Located on the top or side of the foot. A close-up photograph. The contributor is female — 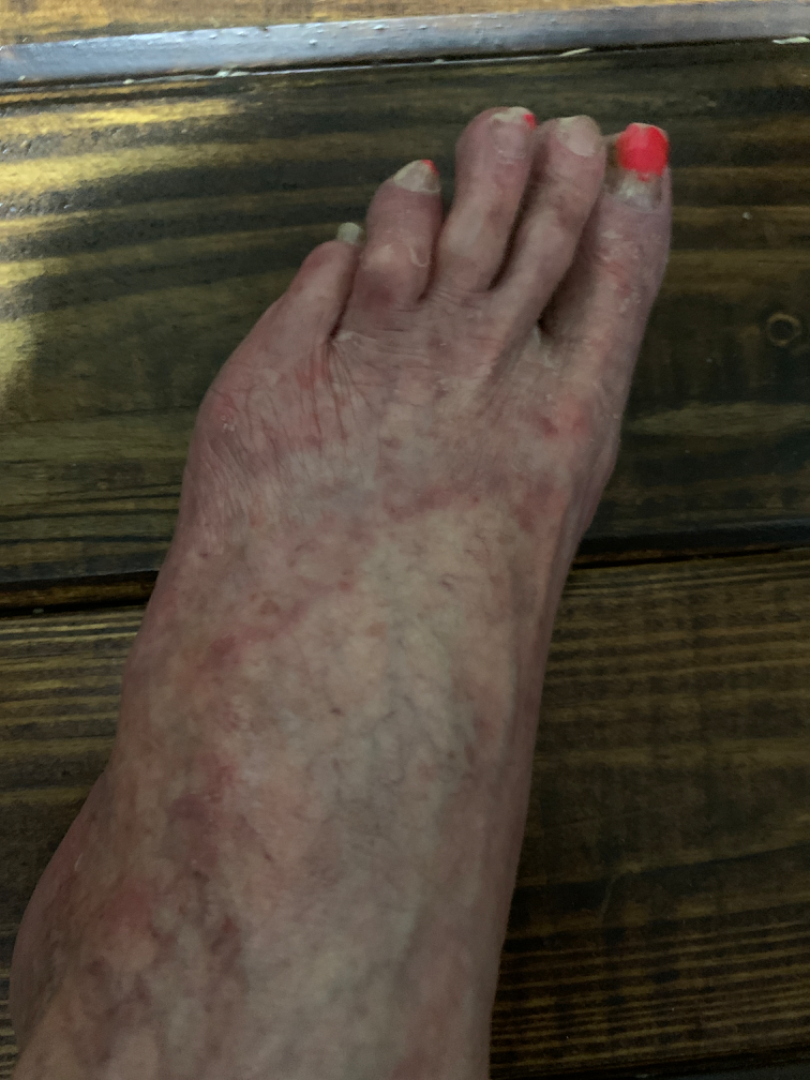Background:
Symptoms reported: bothersome appearance and itching.
Findings:
On dermatologist assessment of the image, consistent with Tinea.